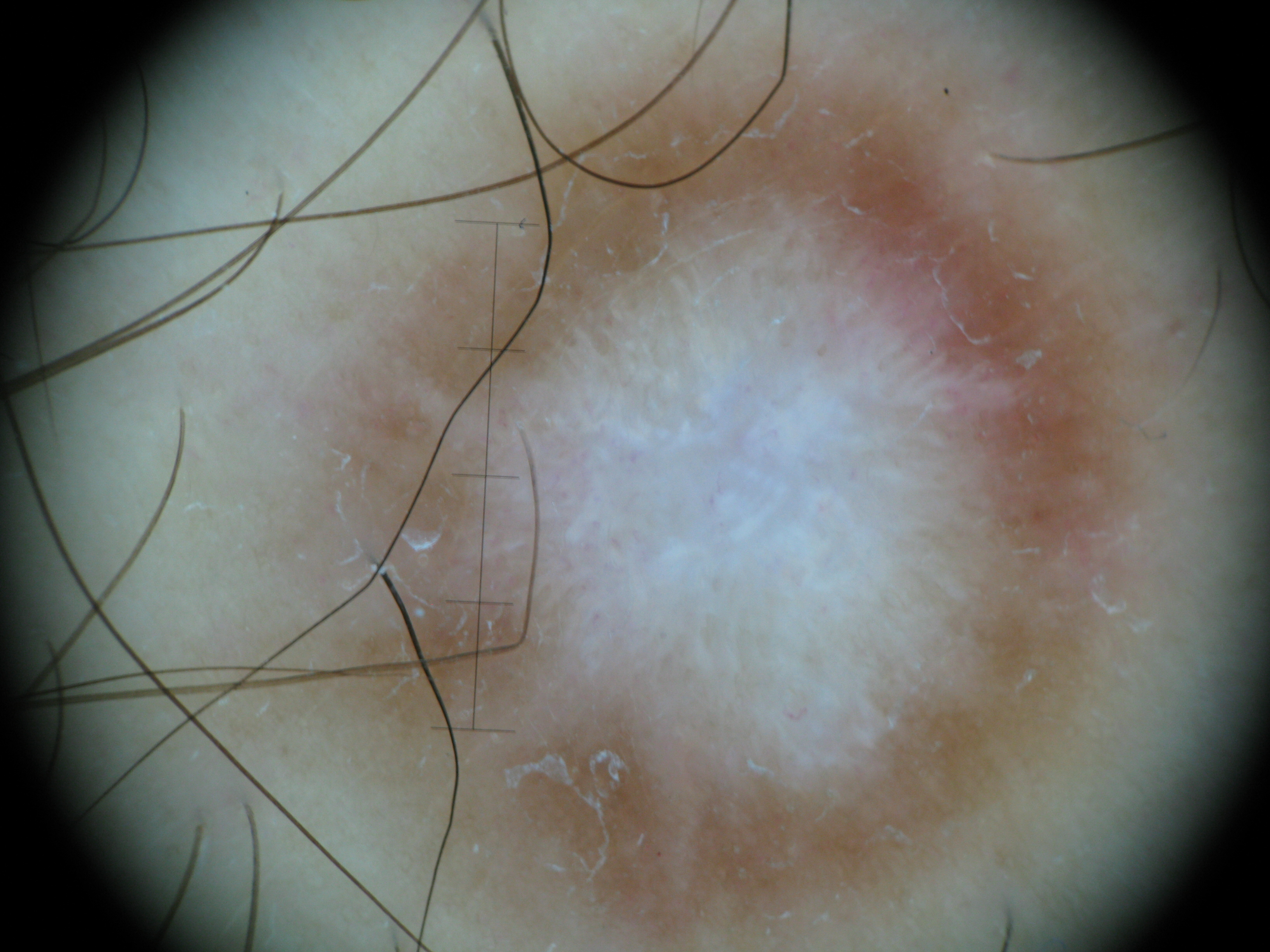Case:
A dermoscopic photograph of a skin lesion.
Conclusion:
Consistent with a fibro-histiocytic lesion — a dermatofibroma.